The photograph is a close-up of the affected area:
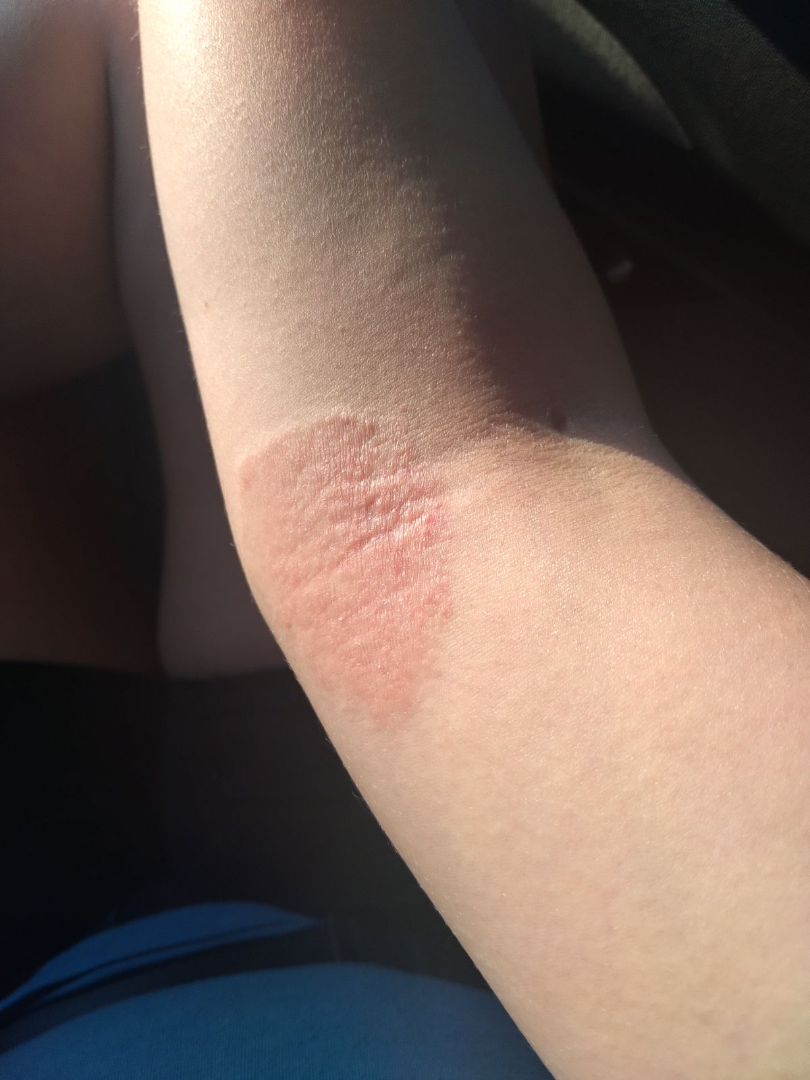Review: Reviewed remotely by one dermatologist: most consistent with Tinea; also consider Majocchi's granuloma; with consideration of Psoriasis.